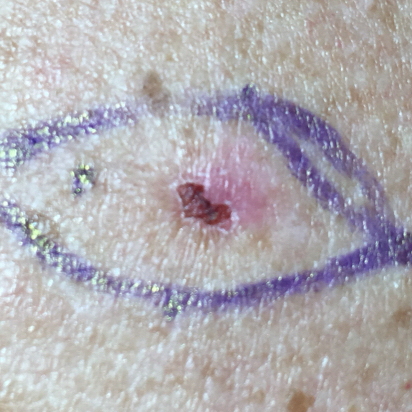The chart records prior malignancy (patient or family).
A clinical photograph of a skin lesion.
A female subject 73 years old.
Fitzpatrick II.
The lesion is on the back.
The lesion measures approximately 8 × 6 mm.
By the patient's account, the lesion hurts, has bled, and itches.
The biopsy diagnosis was a basal cell carcinoma.